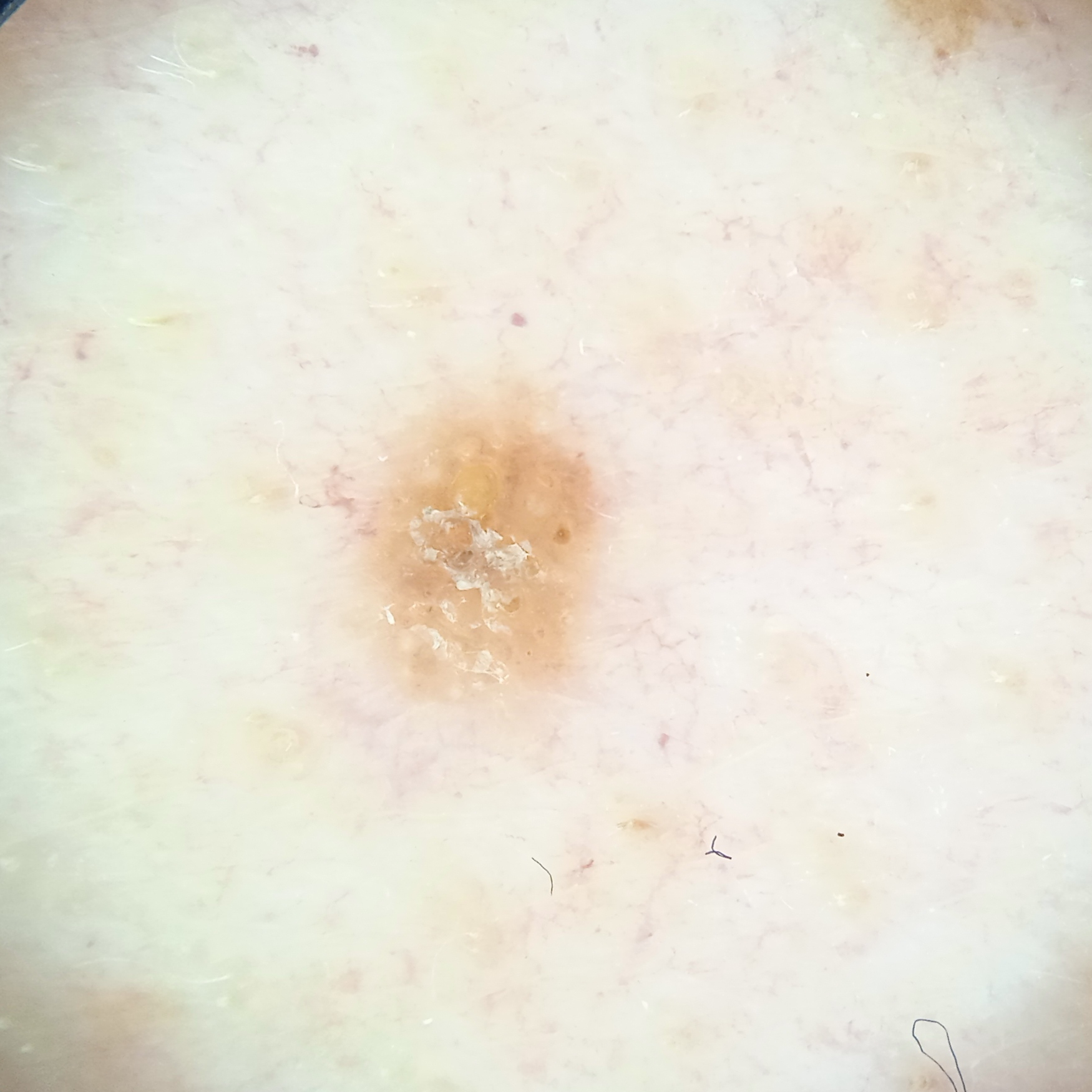diagnostic label = seborrheic keratosis (dermatologist consensus).